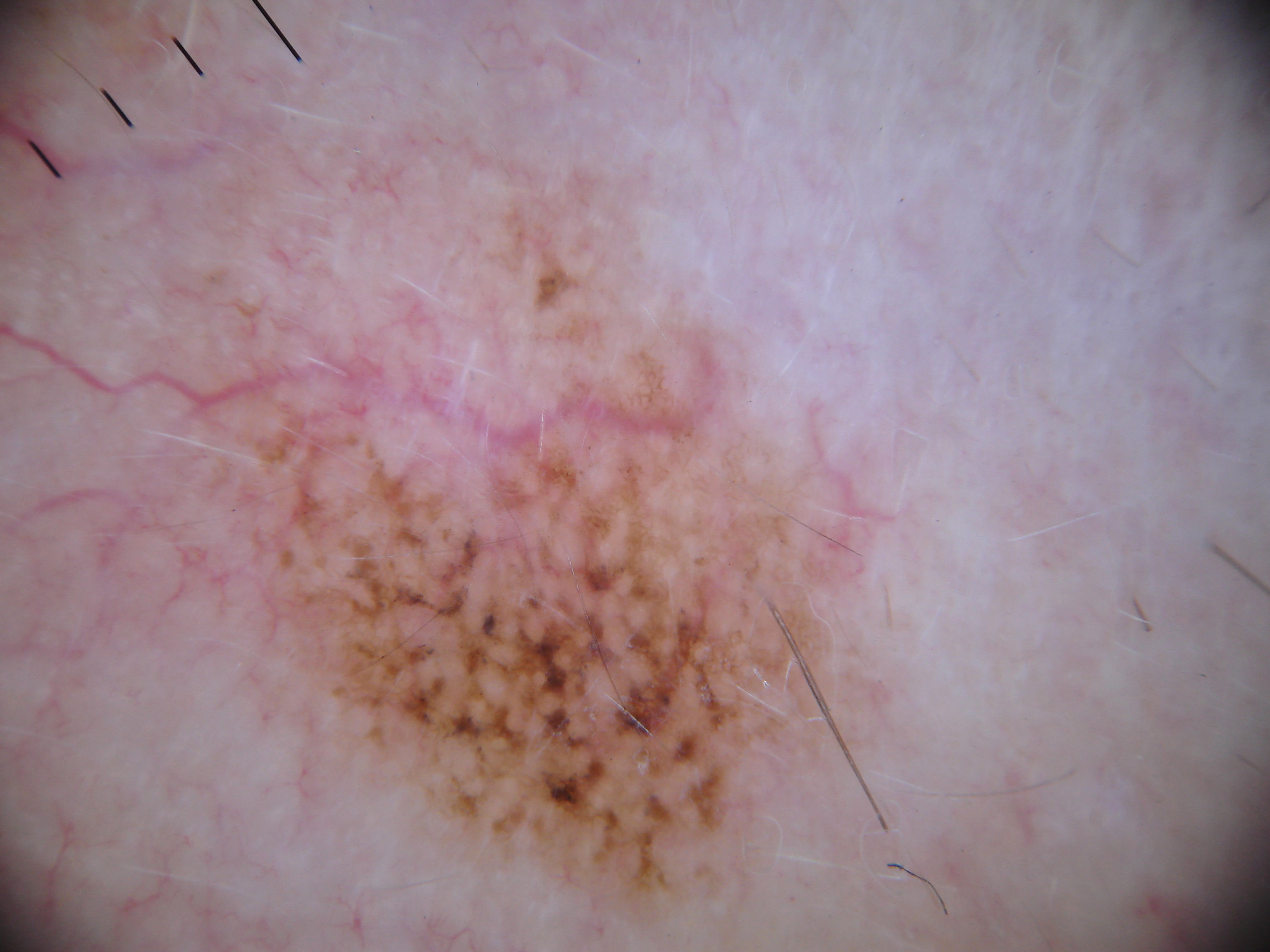A dermoscopic image of a skin lesion.
The lesion is located at left=82, top=103, right=900, bottom=945.
Dermoscopic review identifies globules.
A large lesion occupying much of the field.
On biopsy, the diagnosis was a melanoma.